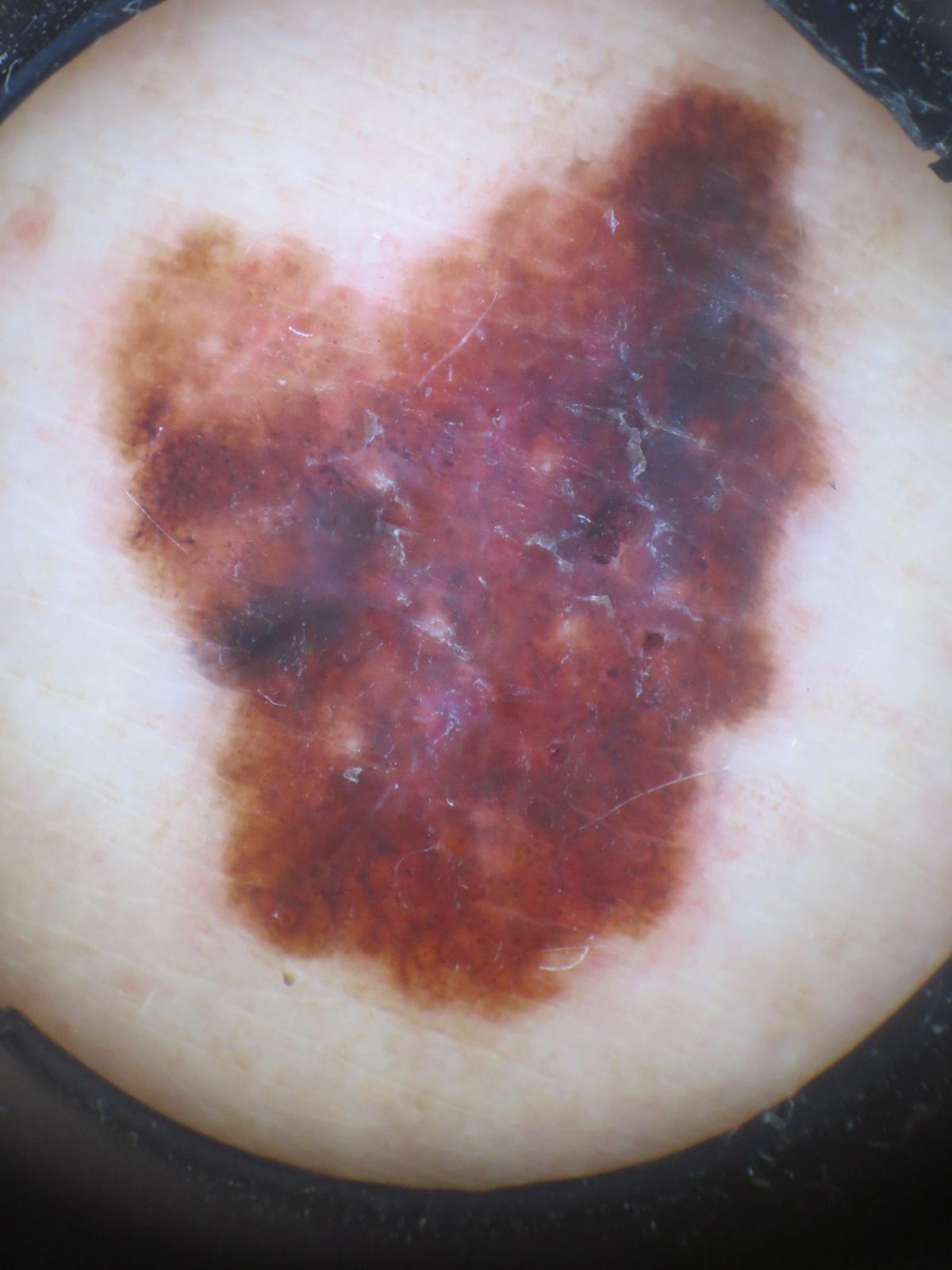risk factors — a prior melanoma | FST — I | image — contact-polarized dermoscopy | subject — female, in their mid-60s | body site — the trunk | diagnosis — Melanoma (biopsy-proven).